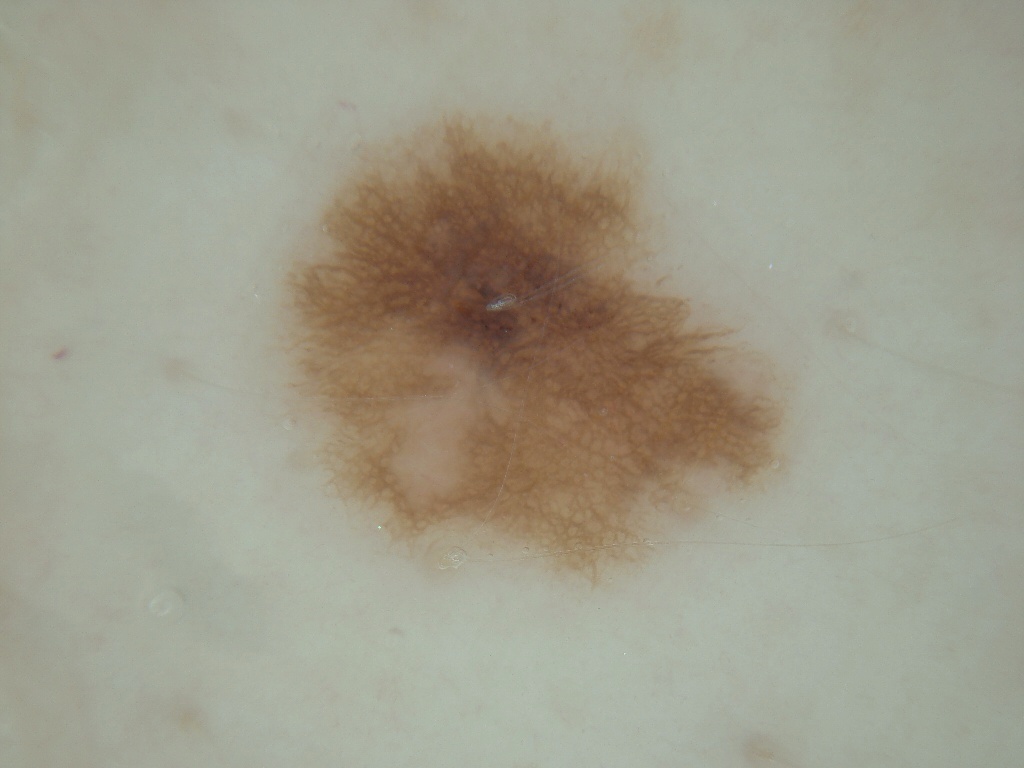Notes:
• patient — female, roughly 55 years of age
• imaging — dermoscopic image
• dermoscopic findings — pigment network; absent: globules, milia-like cysts, streaks, and negative network
• lesion location — [273, 107, 792, 579]
• assessment — a melanocytic nevus